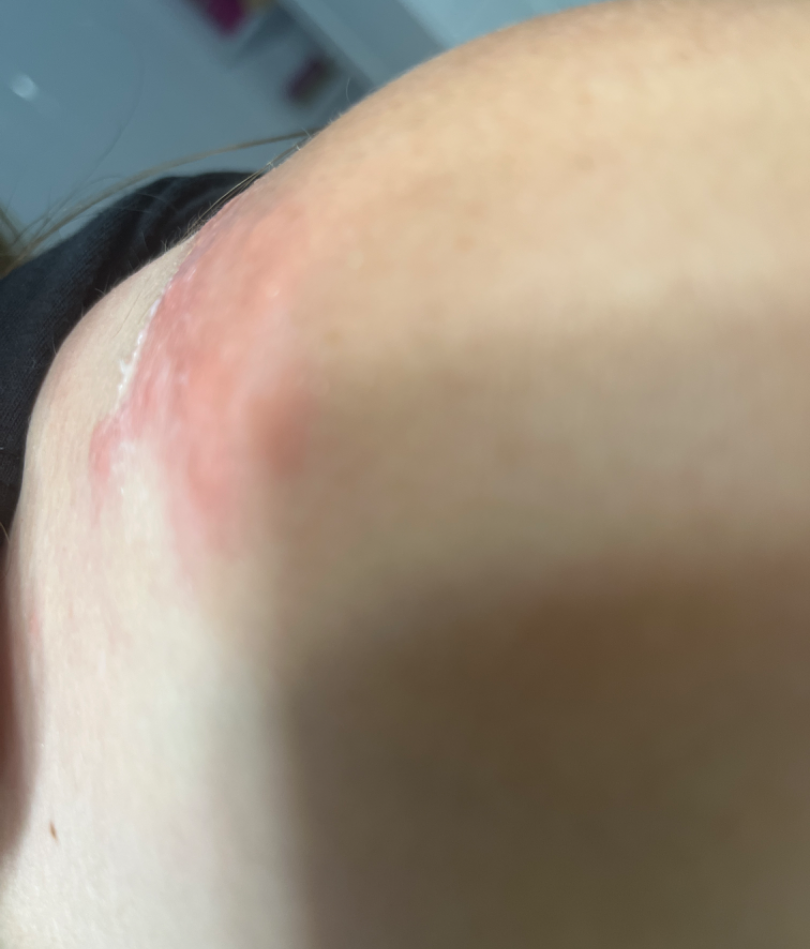Impression: One reviewing dermatologist: favoring Allergic Contact Dermatitis; also on the differential is Insect Bite; also consider Herpes Zoster.